A skin lesion imaged with a dermatoscope.
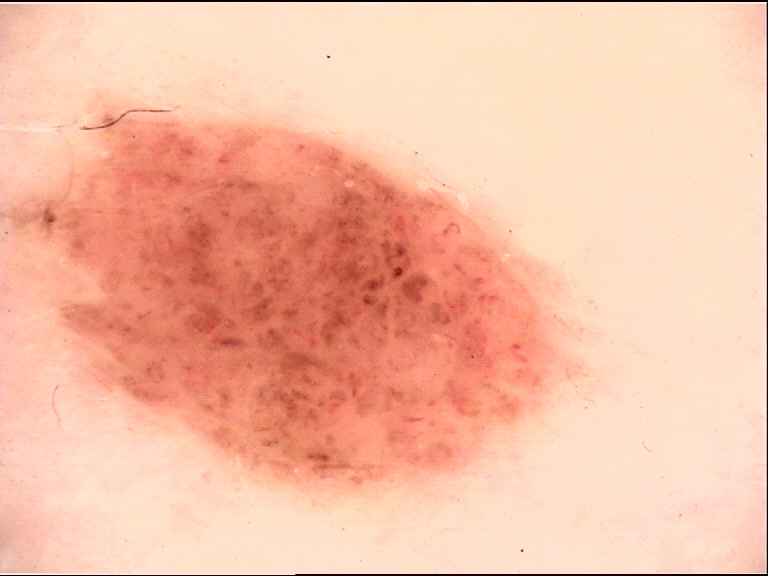diagnostic label — compound nevus (expert consensus).